The contributor reports associated joint pain · reported duration is three to twelve months · the lesion involves the head or neck · symptoms reported: bothersome appearance · texture is reported as flat · the contributor is 50–59, female · this is a close-up image: 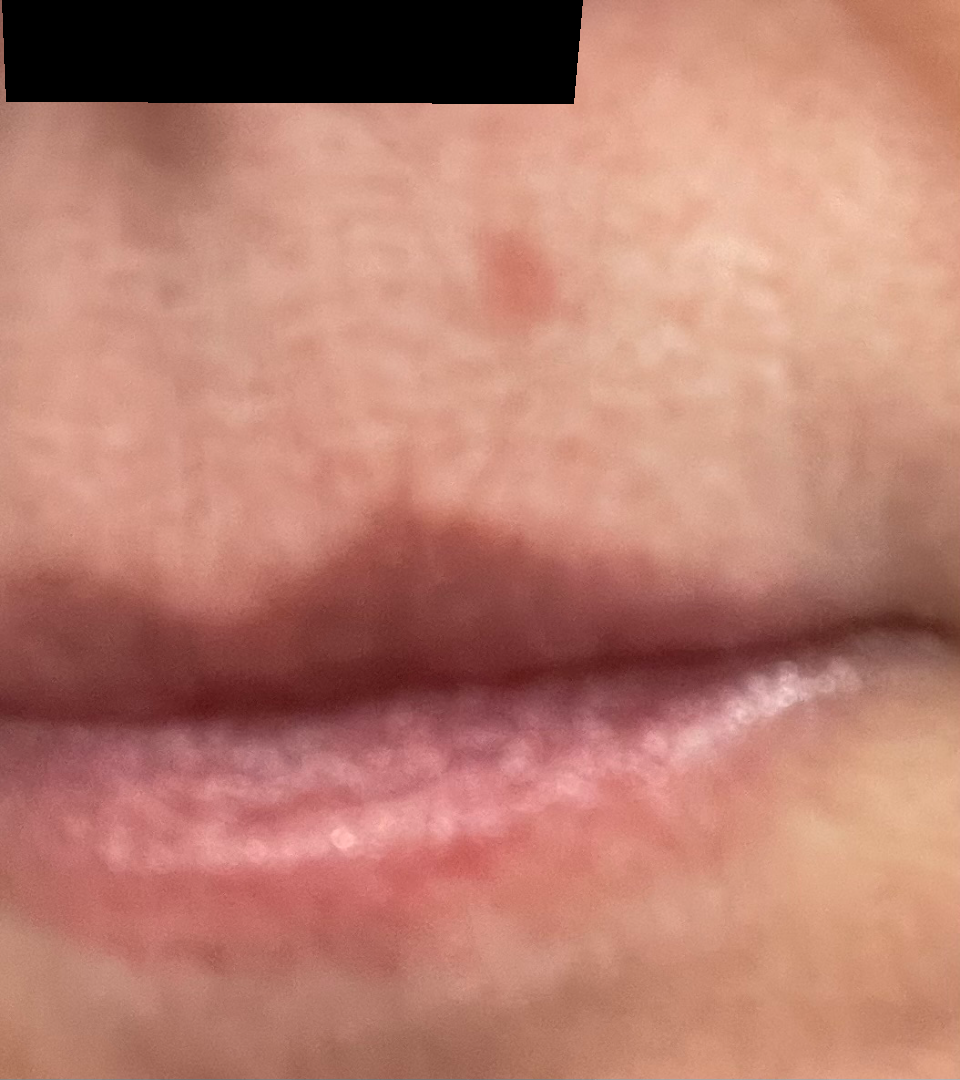Actinic Keratosis (33%); Basal Cell Carcinoma (33%); SCC/SCCIS (33%).